The patient is a female aged 40–49; the lesion is described as raised or bumpy; the patient described the issue as a rash; present for about one day; the photograph was taken at a distance; the lesion involves the arm; symptoms reported: itching.
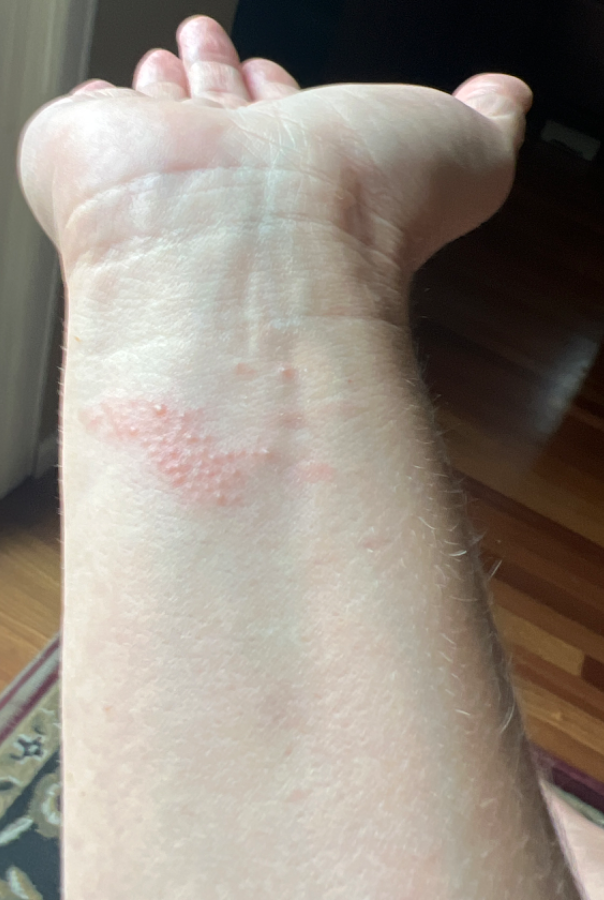{"differential": {"leading": ["Allergic Contact Dermatitis"], "considered": ["Herpes Simplex", "Eczema"], "unlikely": ["Lichen nitidus"]}}